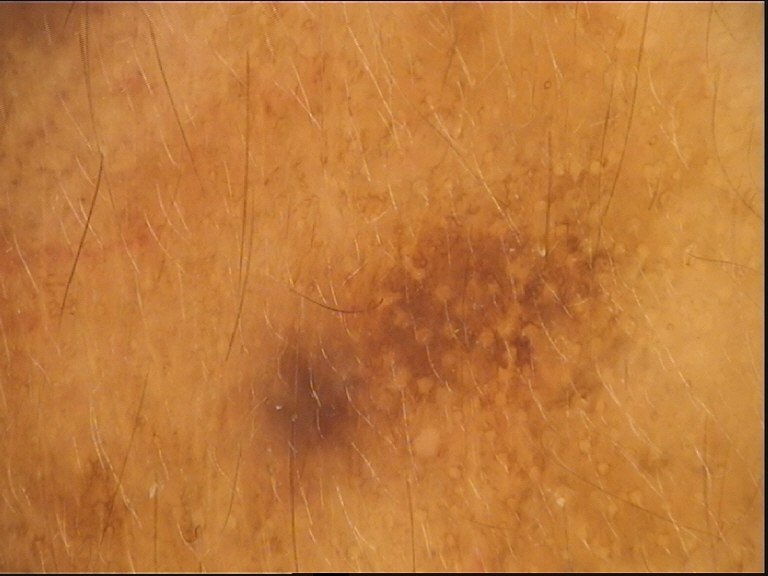The diagnostic label was a dysplastic junctional nevus.